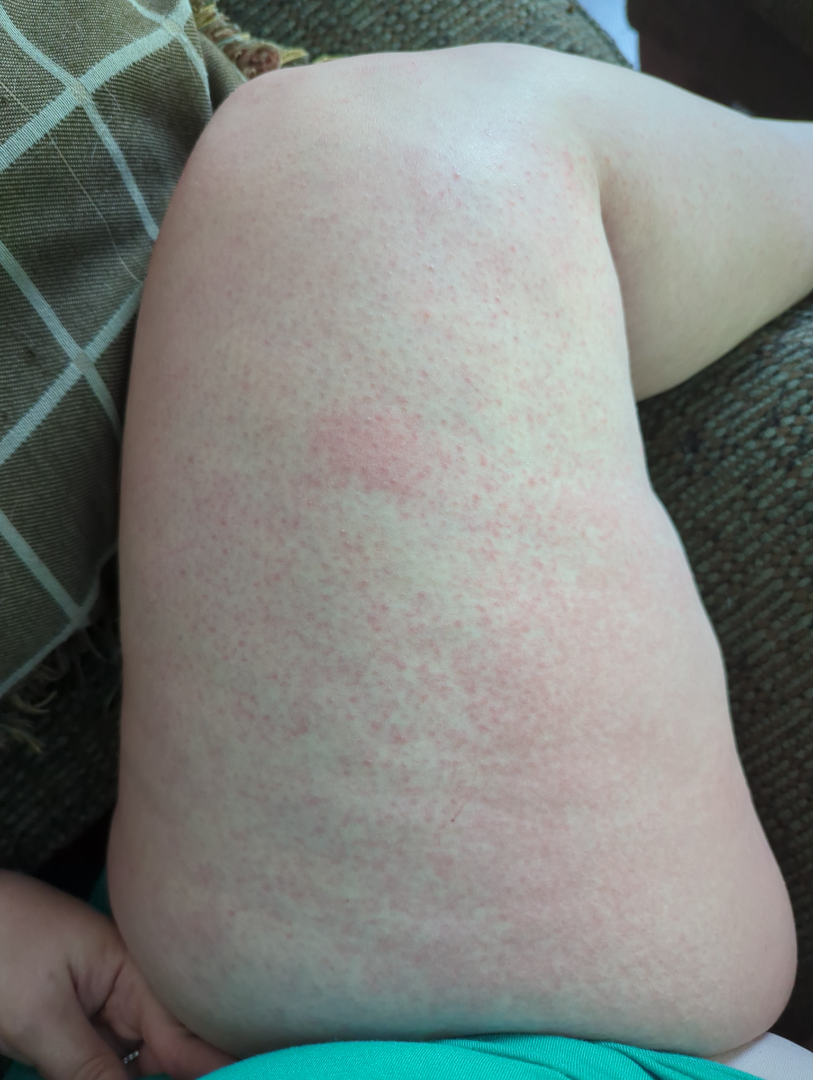* patient-reported symptoms — bothersome appearance
* subject — female, age 30–39
* duration — about one day
* patient's own categorization — a rash
* skin tone — Fitzpatrick II
* texture — flat
* location — leg
* view — at a distance
* impression — Eczema and Drug Rash were considered with similar weight